The lesion involves the leg. The photograph is a close-up of the affected area. Texture is reported as raised or bumpy and rough or flaky. The lesion is associated with burning and itching. The patient notes the condition has been present for less than one week: 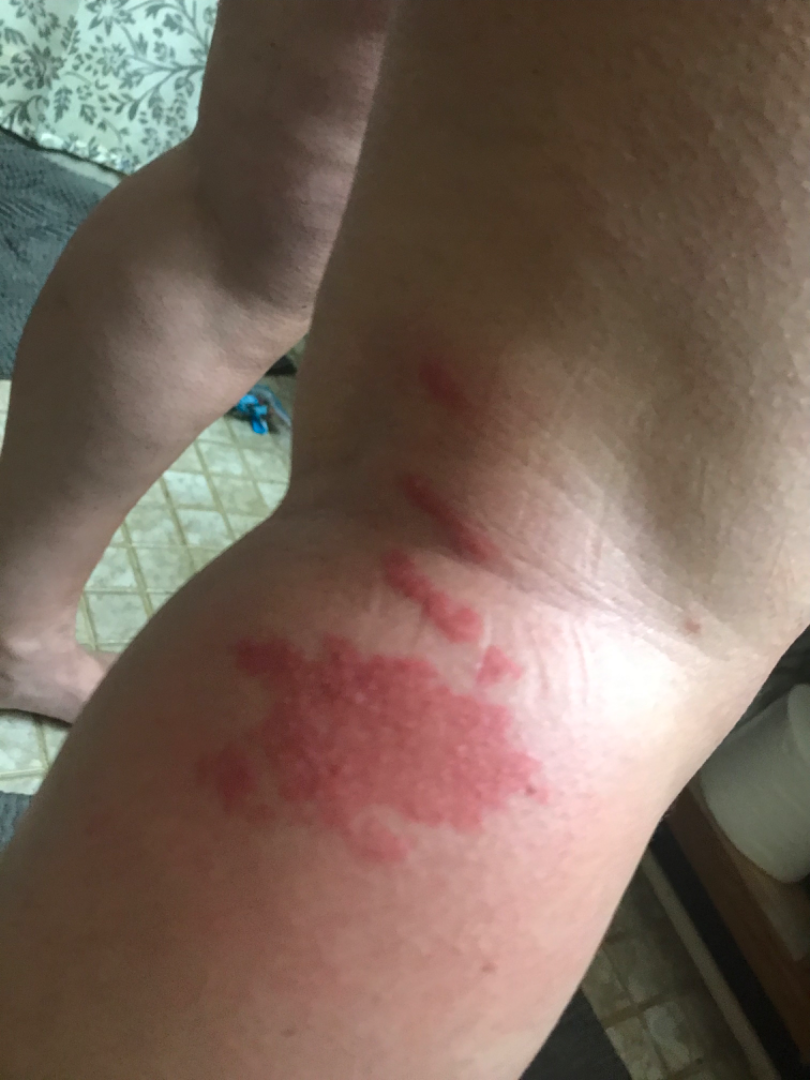The favored diagnosis is Allergic Contact Dermatitis; with consideration of Urticaria; possibly Eczema.